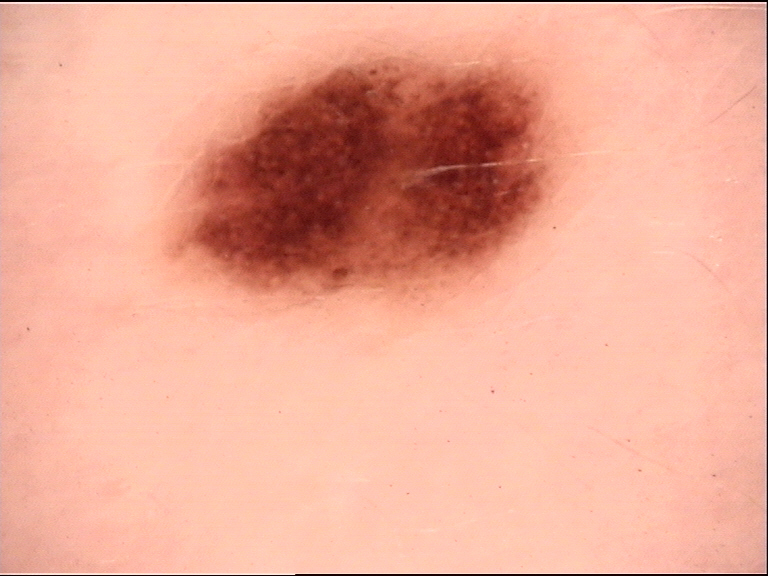Consistent with a dysplastic junctional nevus.